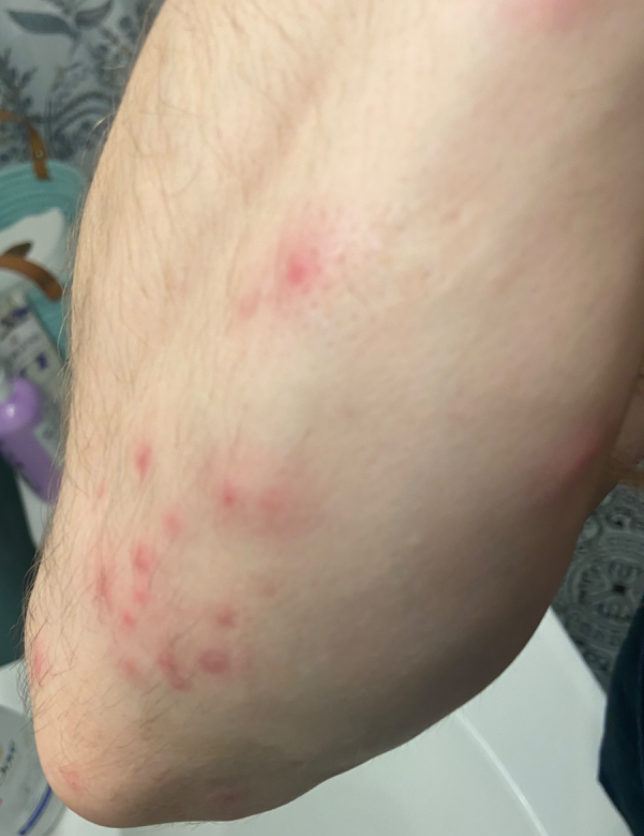  patient: male, age 18–29
  shot_type: at an angle
  body_site: arm
  duration: less than one week
  patient_category: a rash
  texture: raised or bumpy
  symptoms: itching
  differential:
    leading:
      - Insect Bite
    considered:
      - Folliculitis
    unlikely:
      - Granuloma annulare